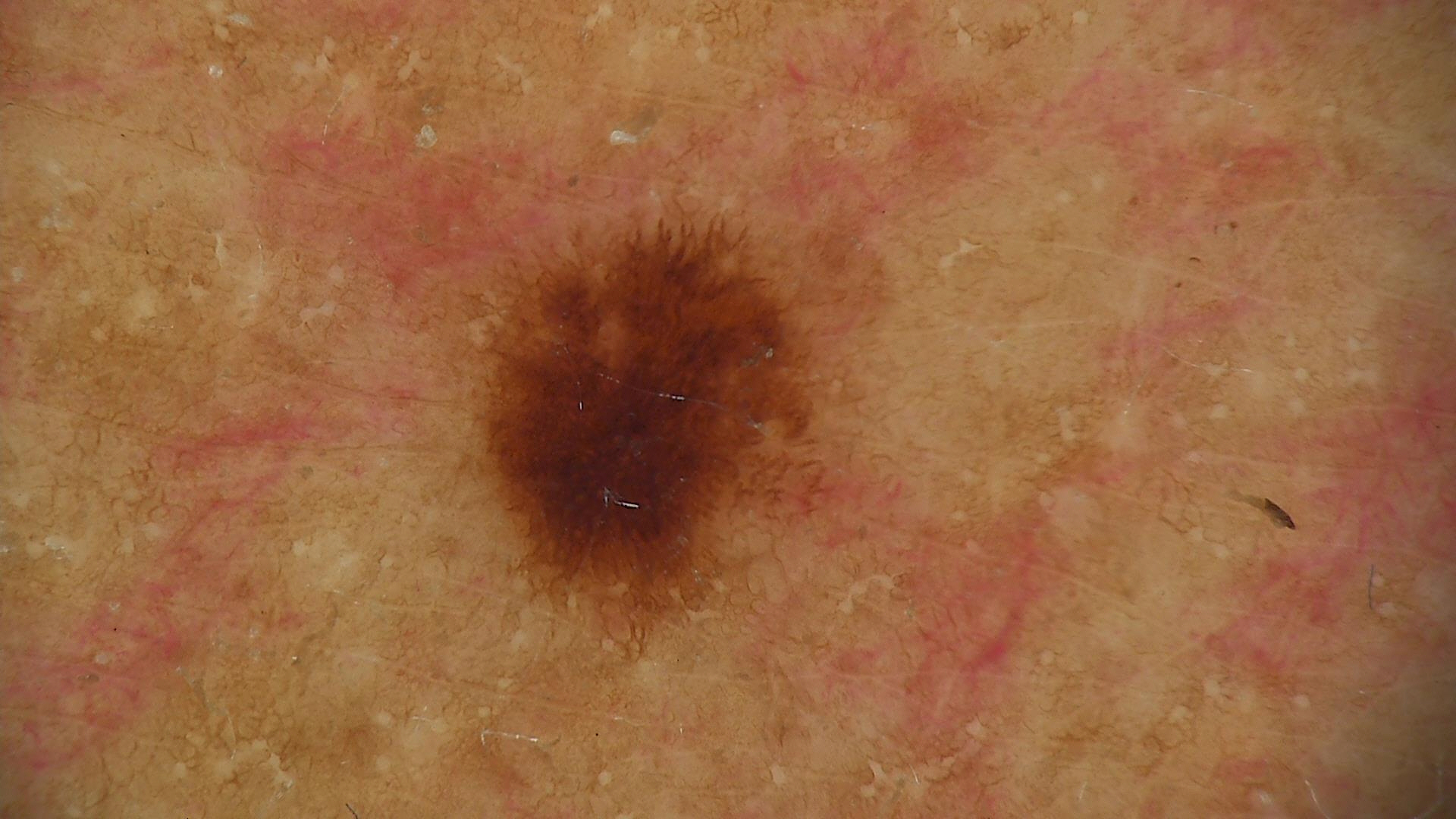image type=dermoscopy
assessment=dysplastic junctional nevus (expert consensus)